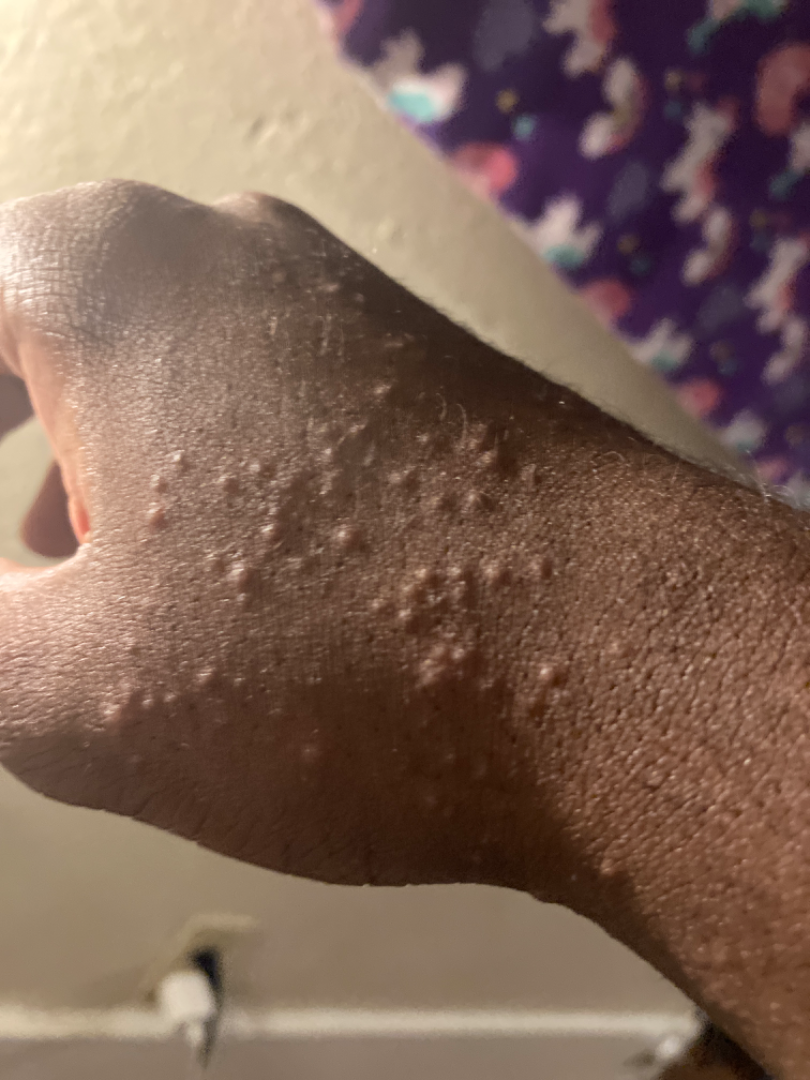assessment: ungradable on photographic review.